A clinical photo of a skin lesion taken with a smartphone; Fitzpatrick skin type II; a male patient aged 43; the chart notes pesticide exposure: 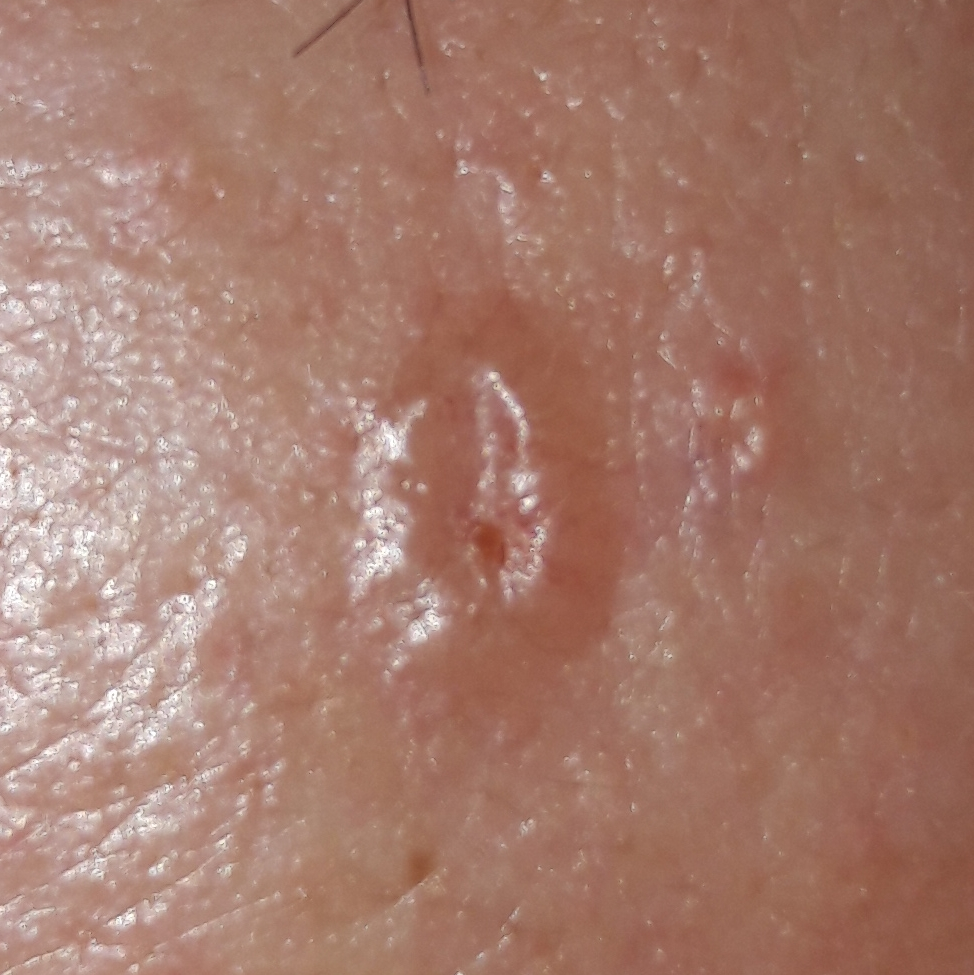The lesion involves the face. The lesion measures approximately 5 × 5 mm. Per patient report, the lesion is elevated, itches, and has grown, but does not hurt and has not bled. Confirmed on histopathology as a basal cell carcinoma.